A dermoscopic photograph of a skin lesion: 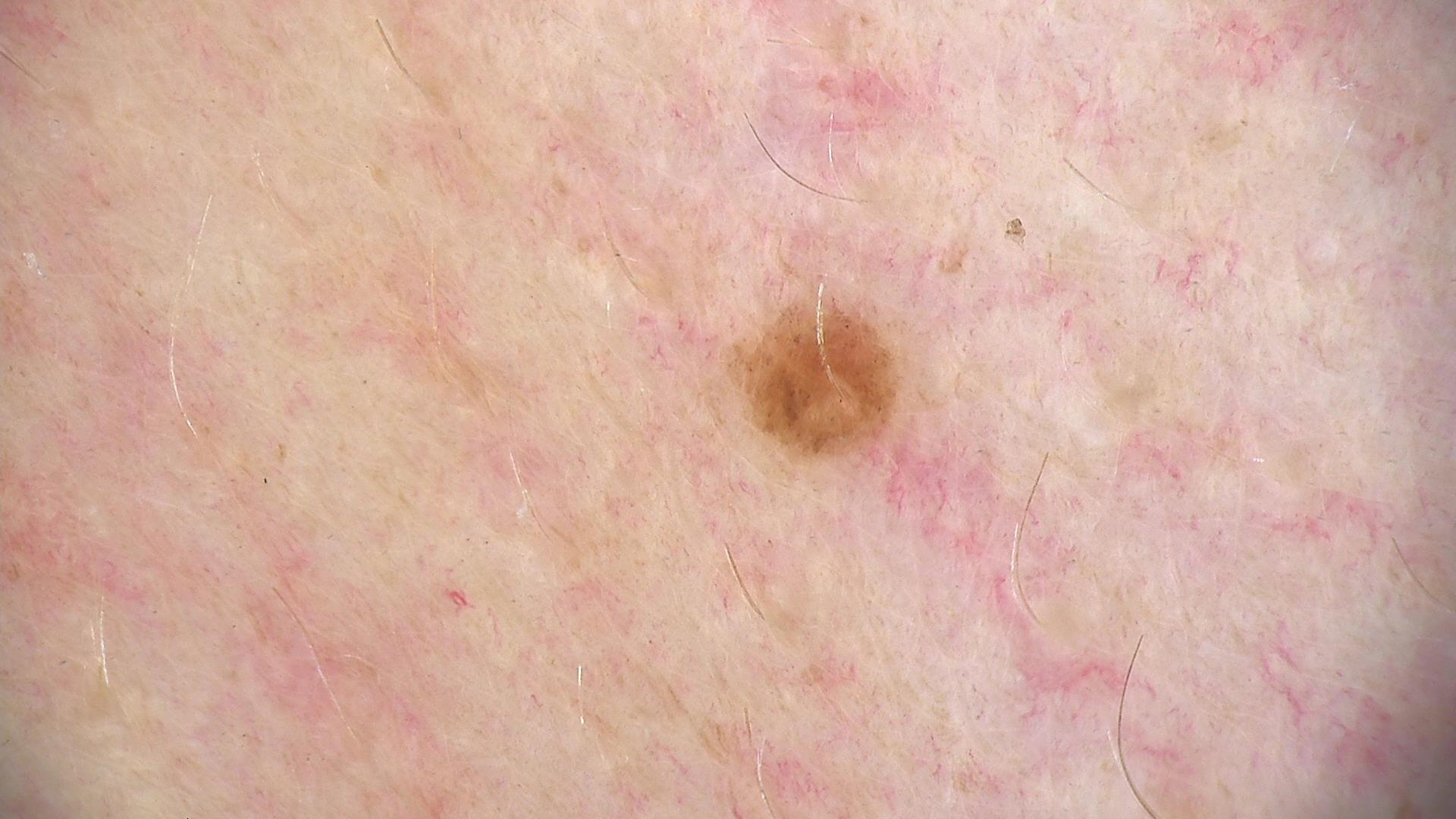Diagnosed as a dysplastic junctional nevus.